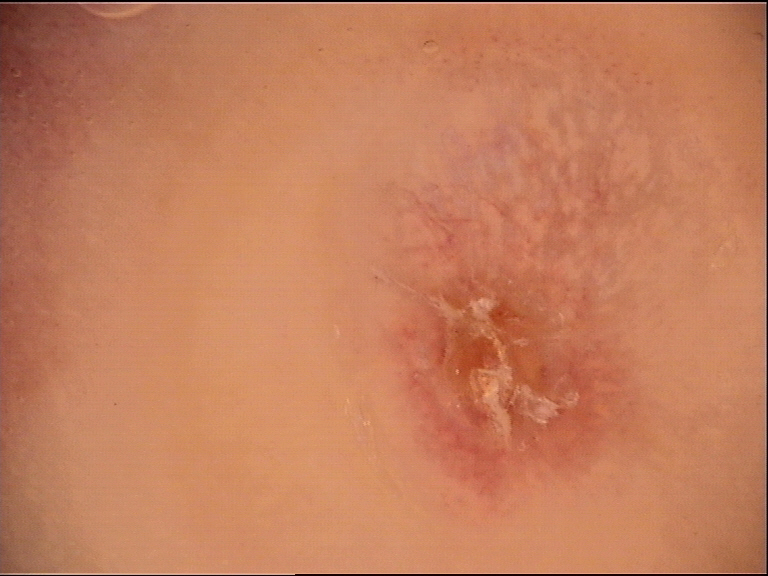Q: What was the diagnostic impression?
A: dermatofibroma (expert consensus)